Acquired for a research image collection, with no referral diagnosis. The patient reports no family history of skin cancer and no personal history of cancer. Few moles overall by the patient's own estimate. A male patient aged 62. The patient says their skin reddens with sun exposure. A dermoscopic image of a skin lesion: 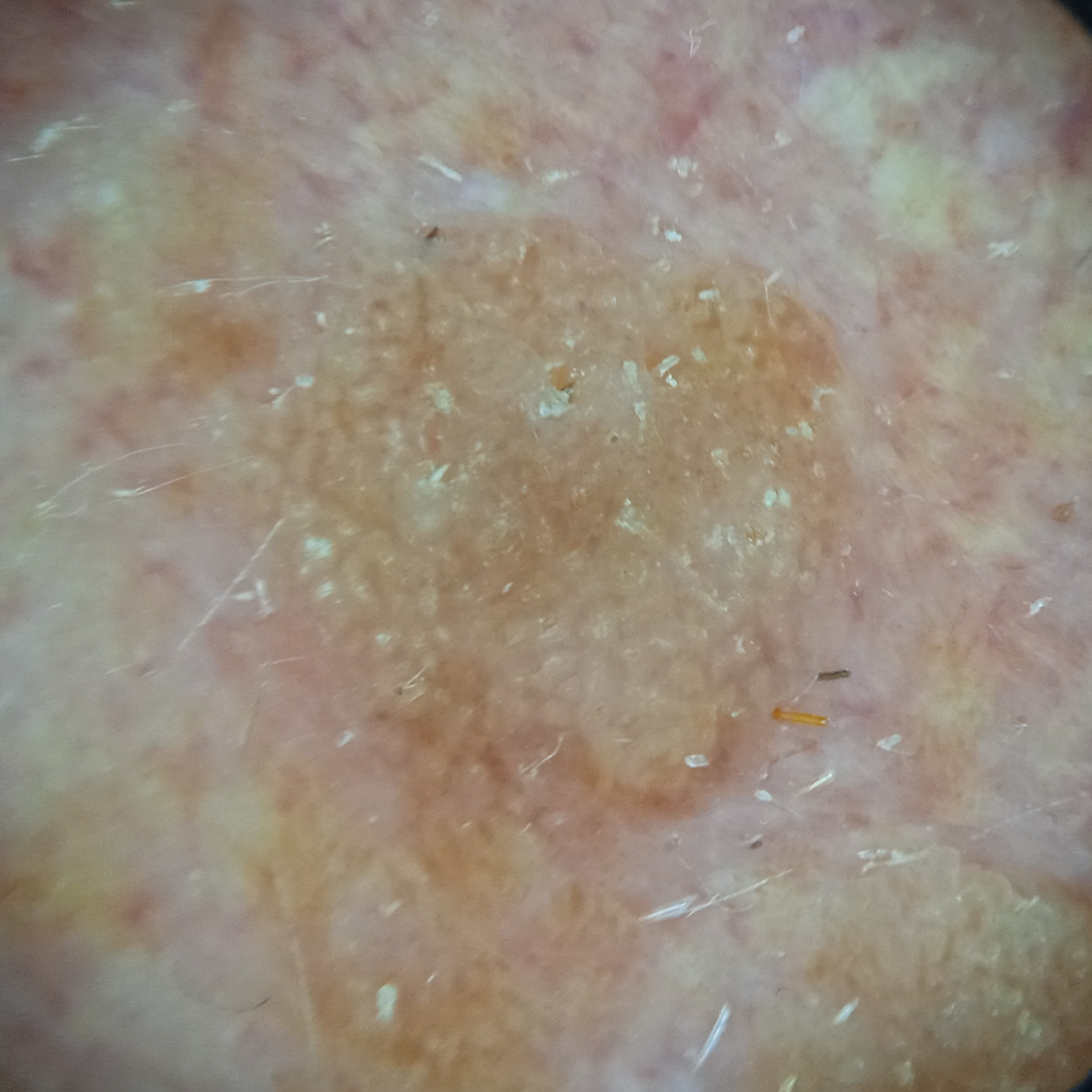  lesion_size:
    diameter_mm: 7.5
  diagnosis:
    name: seborrheic keratosis
    malignancy: benign